A clinical photograph showing a skin lesion; on a questionnaire the patient reported a personal history of cancer; the patient says their skin tans without first burning; a female patient aged 84; referred with a clinical suspicion of basal cell carcinoma: 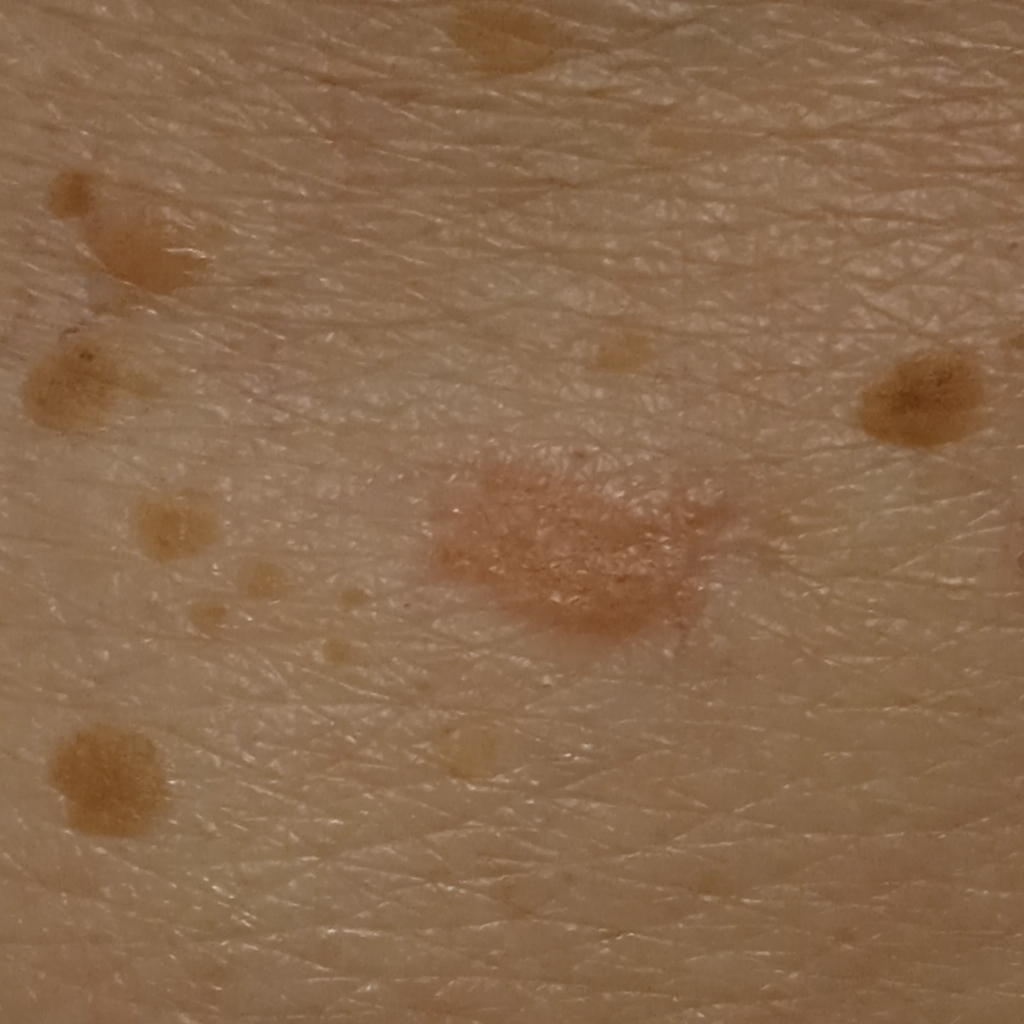Findings:
The lesion is on the torso. The lesion measures approximately 12.5 mm.
Conclusion:
Histopathology confirmed a basal cell carcinoma, following a punch biopsy, with a measured thickness of 2 mm.